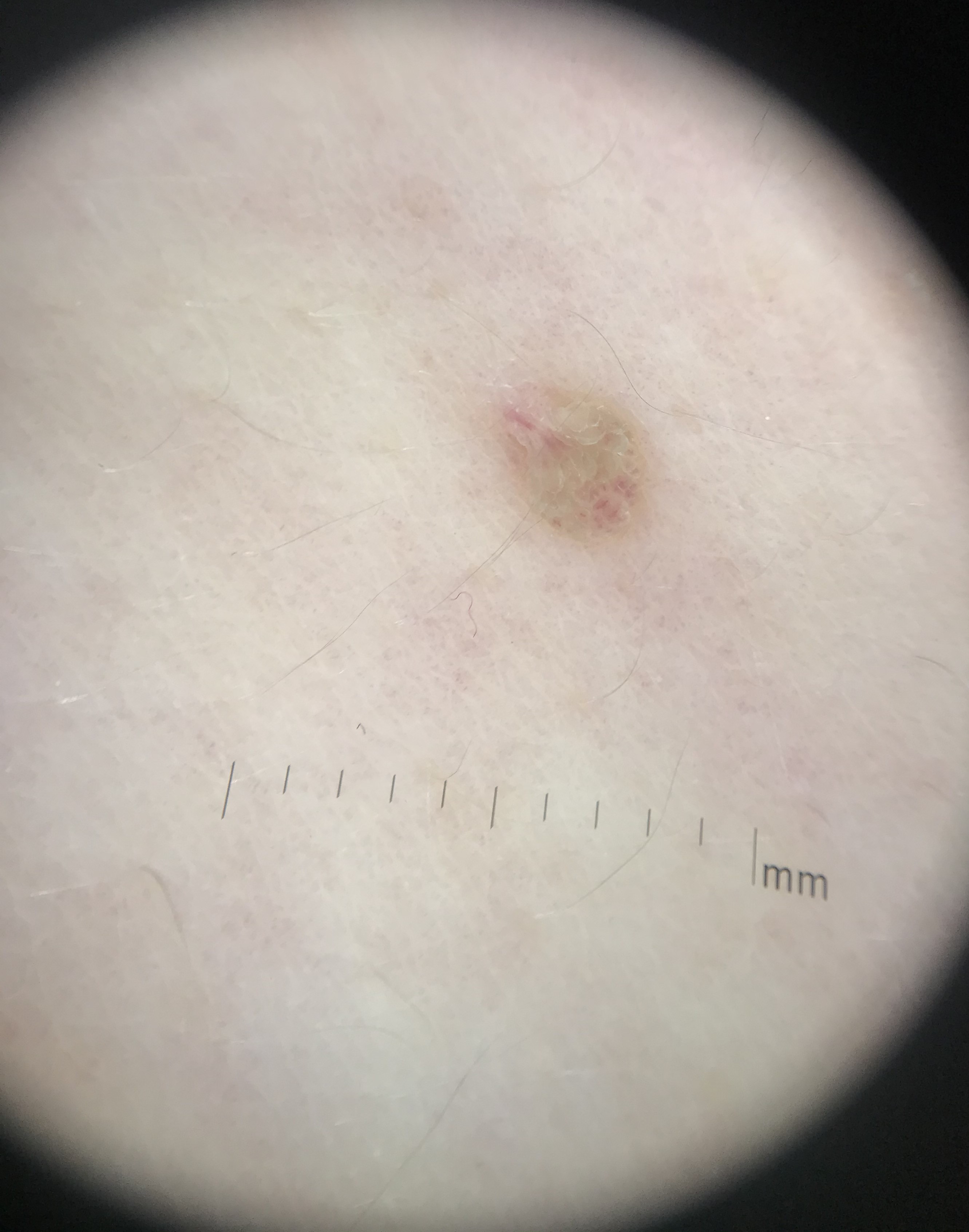image type = dermatoscopy
subtype = keratinocytic
diagnosis = seborrheic keratosis (expert consensus)